A skin lesion imaged with a dermatoscope.
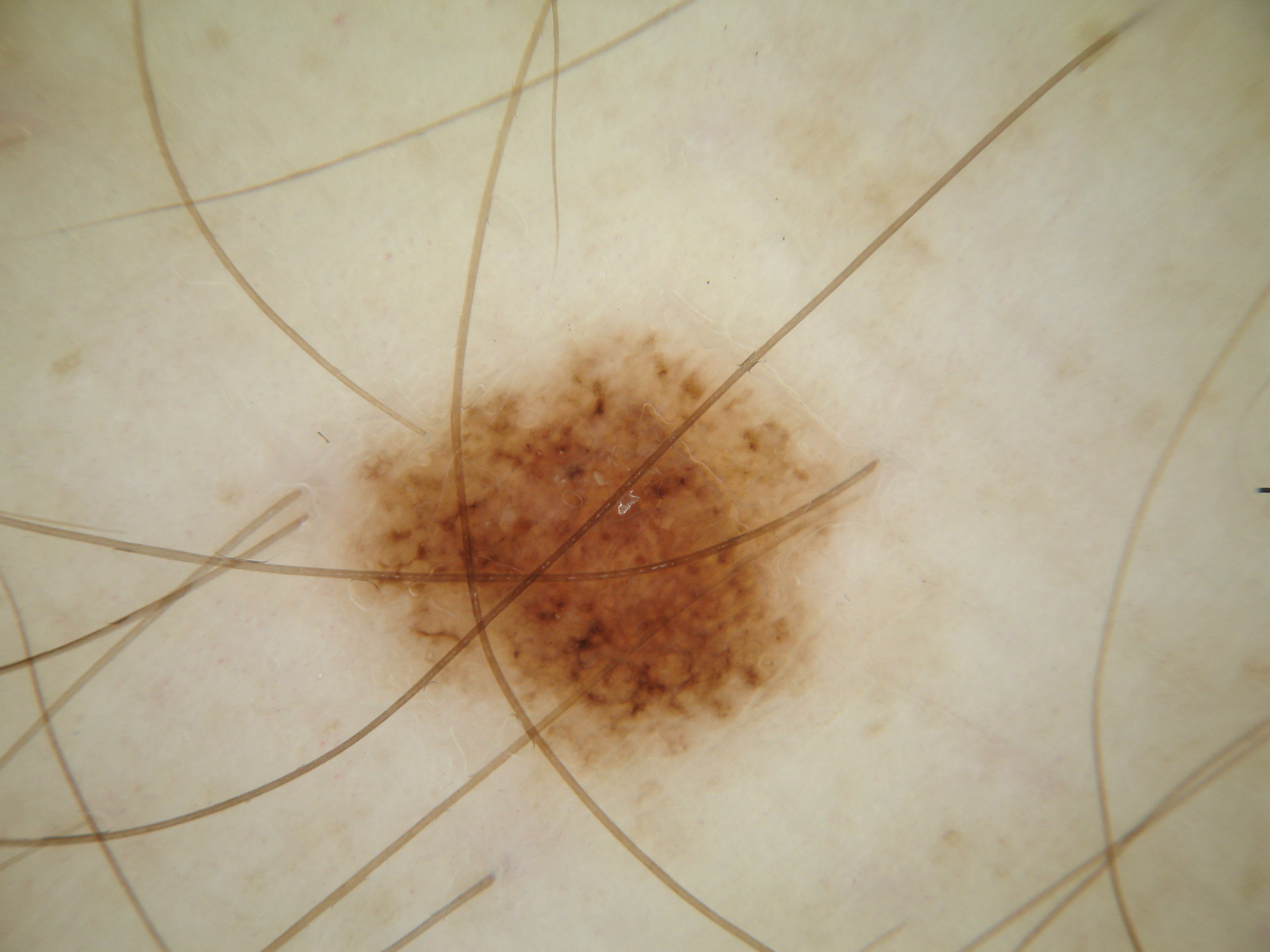The dermoscopic pattern shows pigment network and globules, with no streaks, milia-like cysts, or negative network. Lesion location: box(327, 304, 878, 811). Diagnosed as a melanocytic nevus.